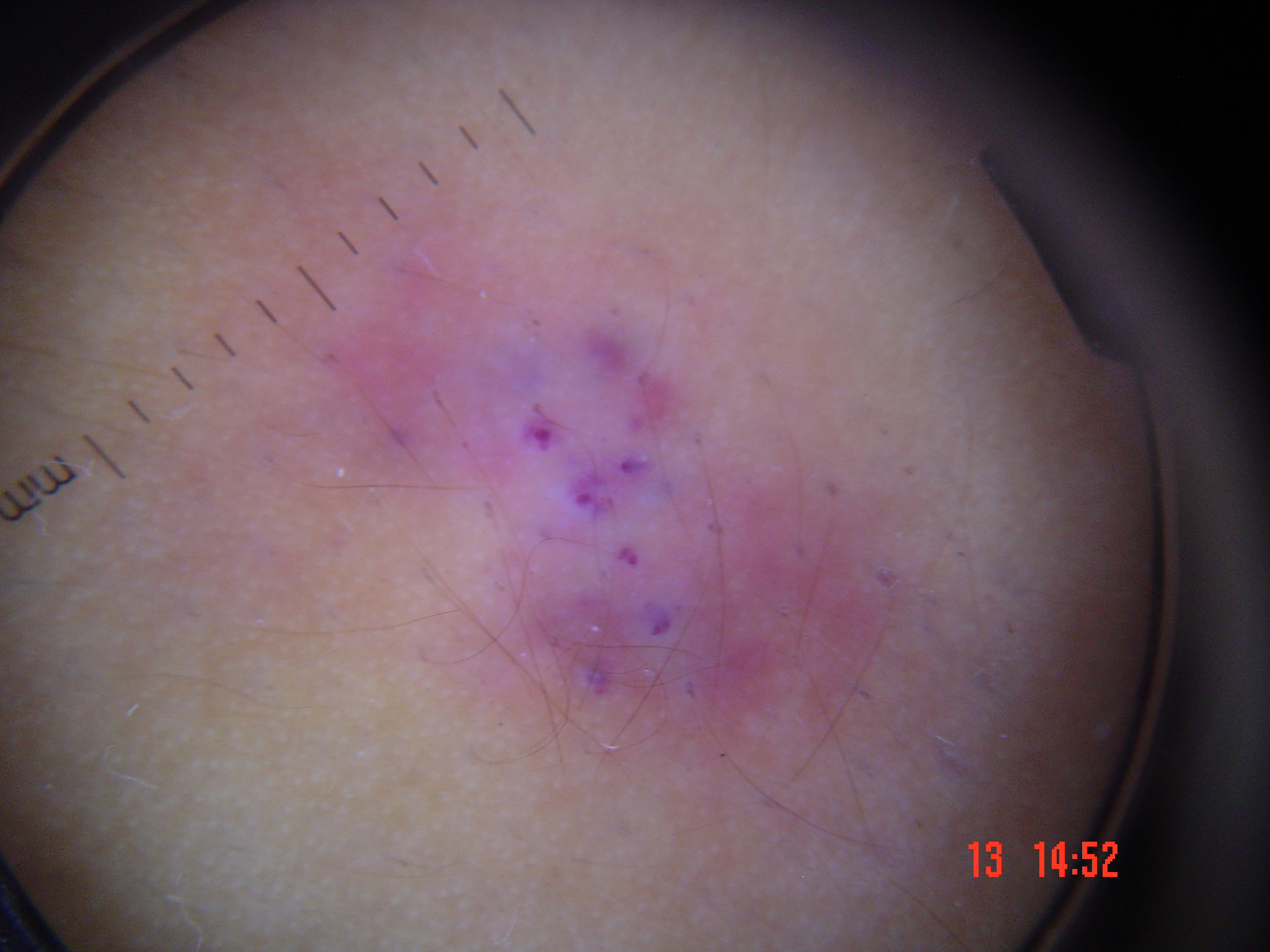label: angiokeratoma (expert consensus).